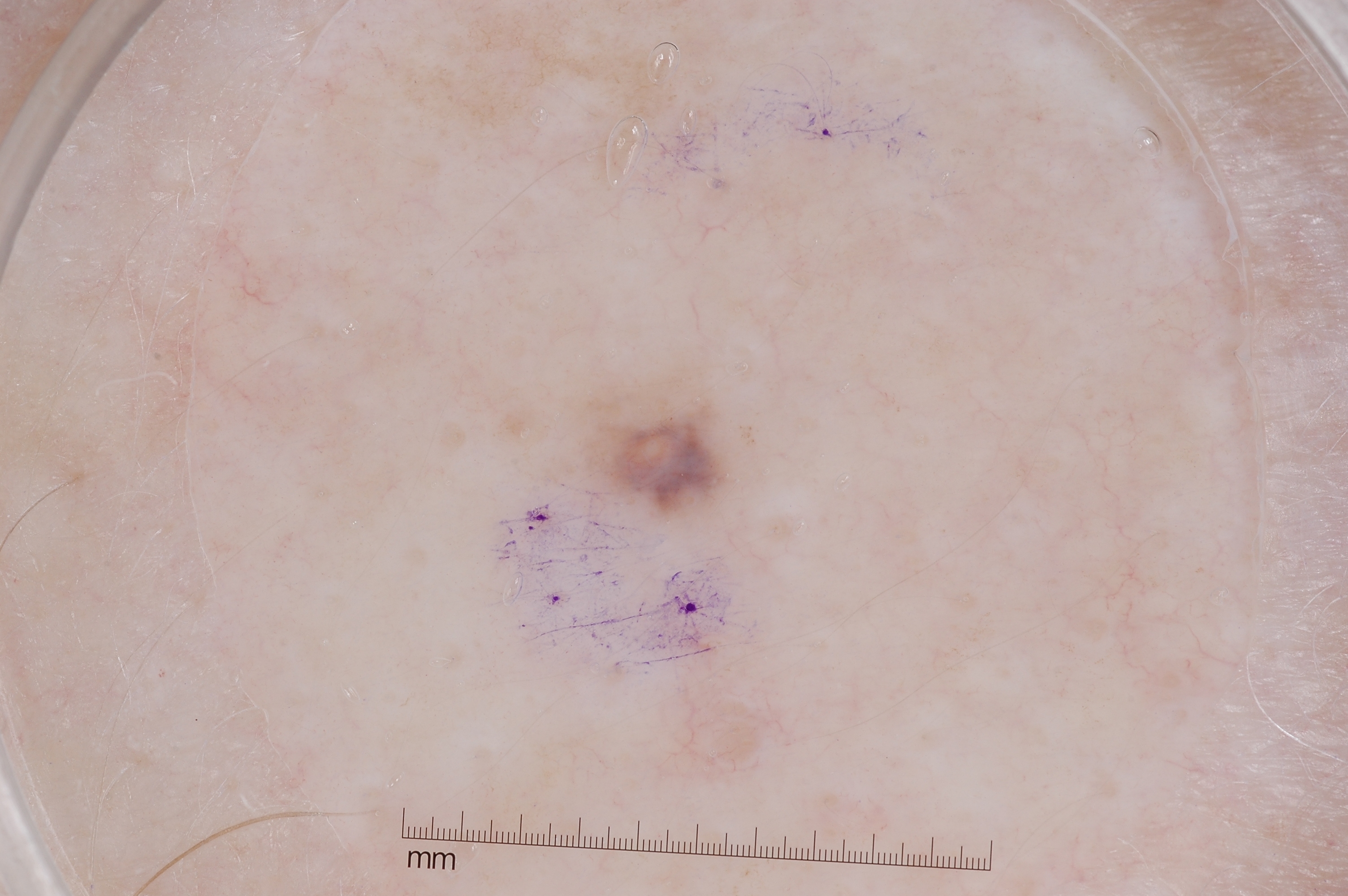A dermoscopic view of a skin lesion. A female subject roughly 65 years of age. The lesion spans bbox=[590, 378, 737, 511]. Dermoscopy demonstrates no pigment network, milia-like cysts, negative network, or streaks. Clinically diagnosed as a melanocytic nevus, a benign skin lesion.